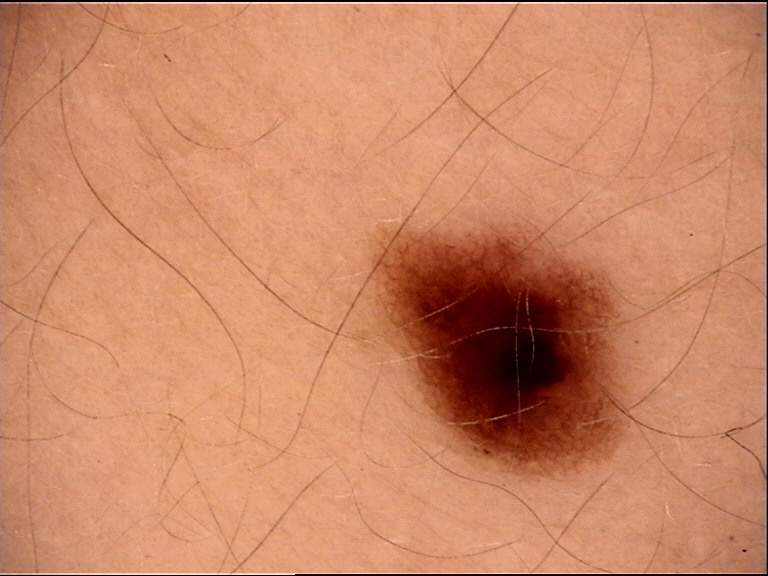Conclusion: The diagnostic label was a dysplastic junctional nevus.